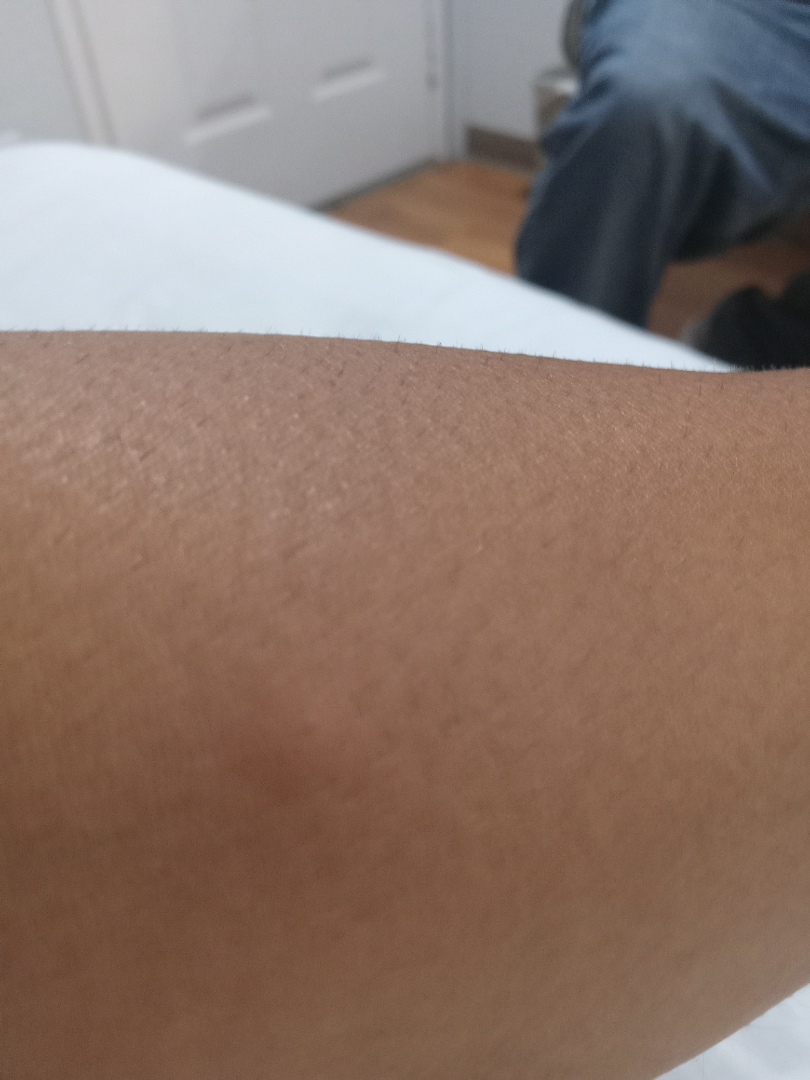The reviewing dermatologist was unable to assign a differential diagnosis from the image.
The photograph is a close-up of the affected area.